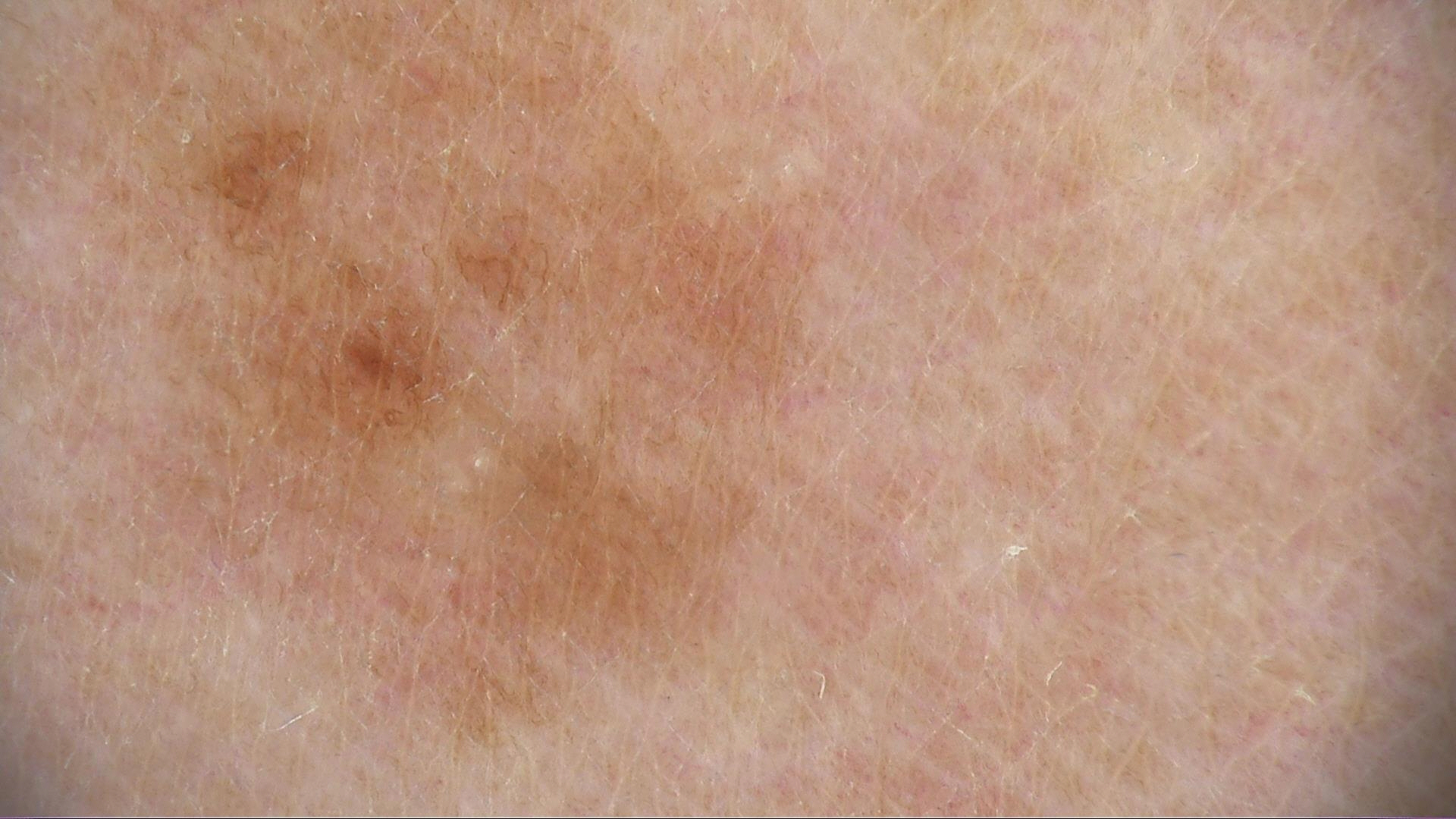| feature | finding |
|---|---|
| assessment | dysplastic junctional nevus (expert consensus) |